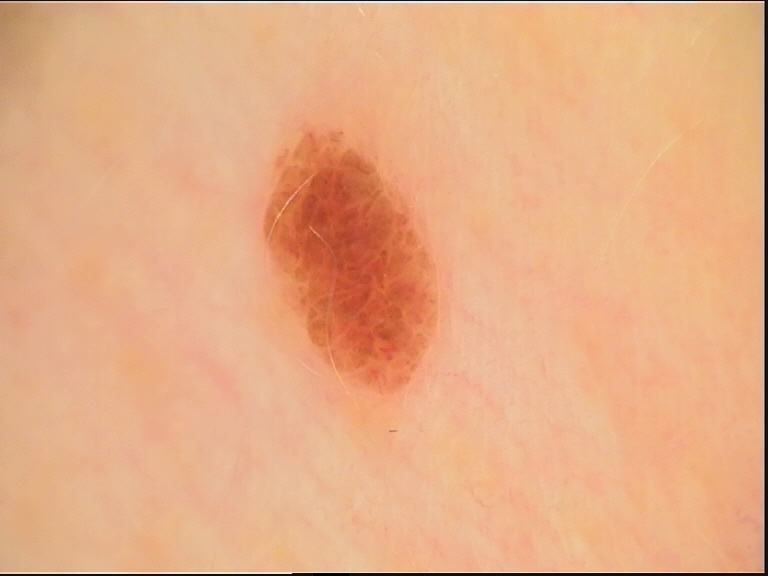Findings:
- assessment: dysplastic compound nevus (expert consensus)